A dermoscopy image of a single skin lesion: 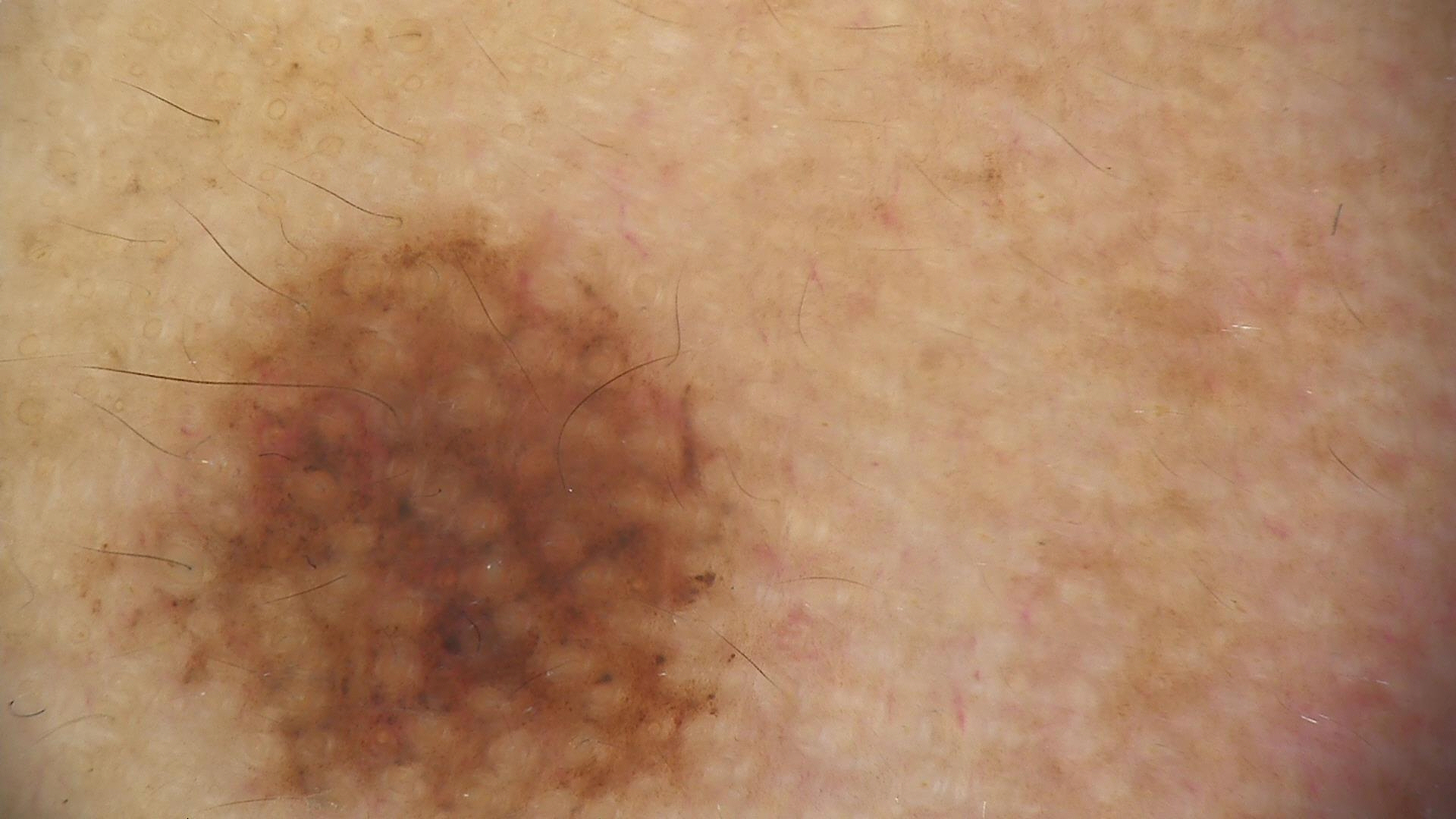Consistent with a banal lesion — a Miescher nevus.